A female subject · a dermoscopy image of a single skin lesion.
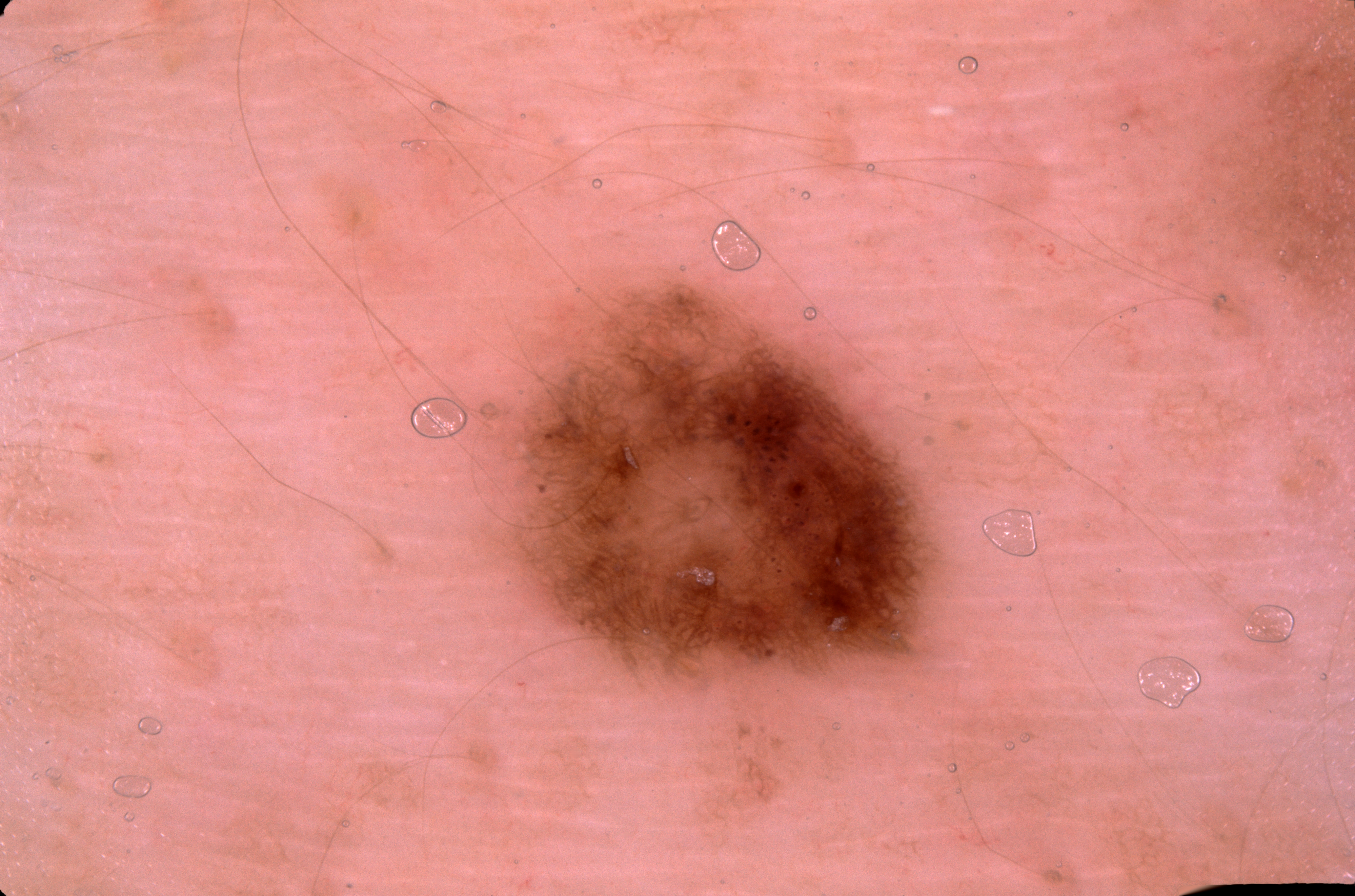In (x1, y1, x2, y2) order, the lesion is bounded by [519,287,931,686]. Dermoscopy demonstrates pigment network; no milia-like cysts, negative network, or streaks. Clinically diagnosed as a melanocytic nevus.